A dermoscopic image of a skin lesion.
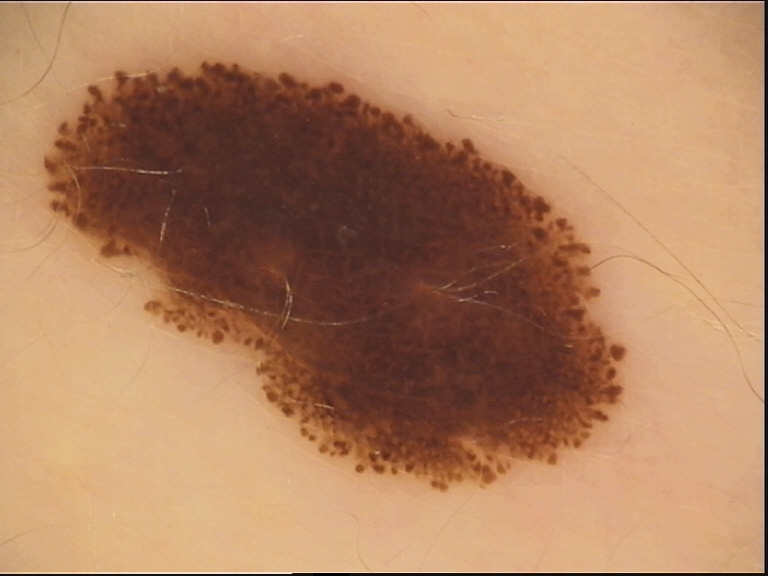Diagnosed as a benign lesion — a dysplastic junctional nevus.